A dermoscopic image of a skin lesion.
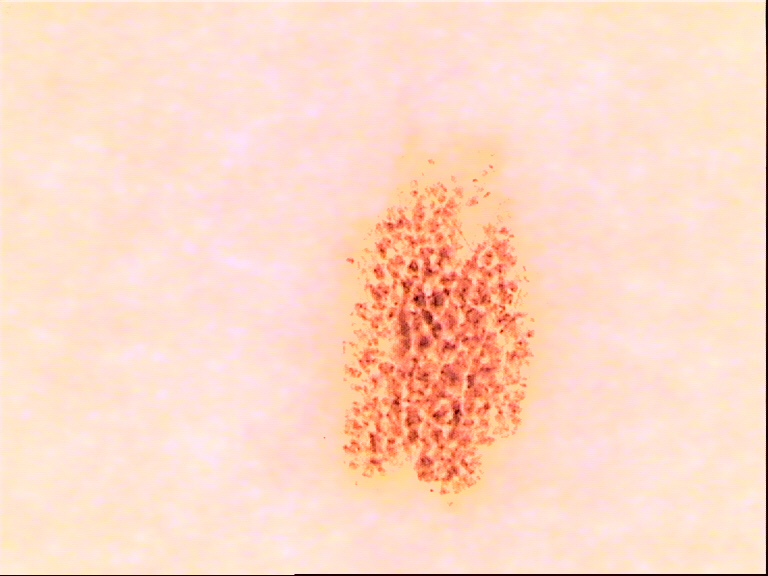Impression:
Diagnosed as a dysplastic compound nevus.